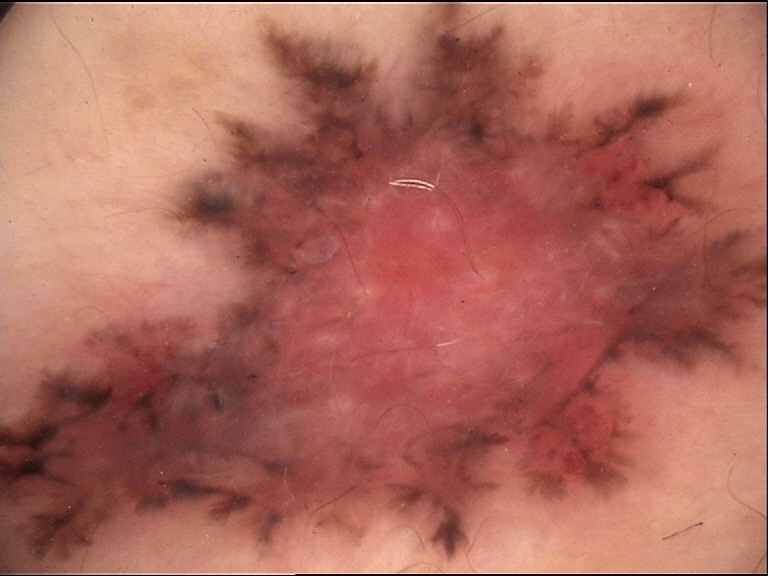Histopathology confirmed a basal cell carcinoma.